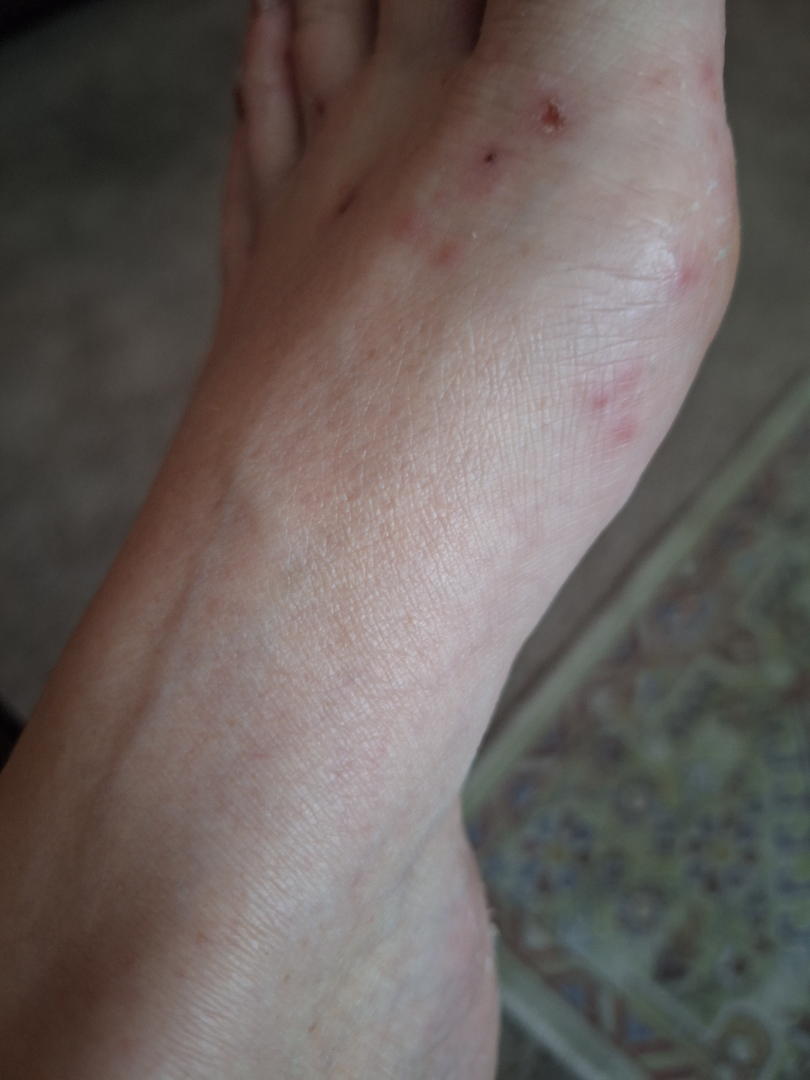A close-up photograph. Chilblain, Insect Bite and Eczema were considered with similar weight.